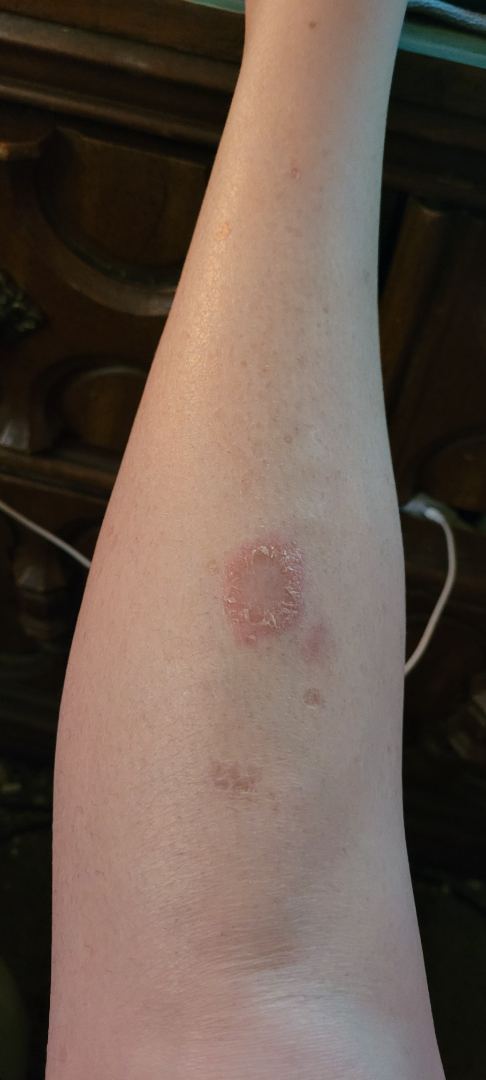Q: What was the assessment?
A: unable to determine
Q: How does the lesion feel?
A: raised or bumpy and rough or flaky
Q: Any systemic symptoms?
A: joint pain, mouth sores, chills and fatigue
Q: When did this start?
A: more than one year
Q: What is the affected area?
A: leg
Q: Image view?
A: at a distance
Q: Reported symptoms?
A: enlargement and bothersome appearance
Q: What is the patient's skin tone?
A: human graders estimated a Monk Skin Tone of 2